The patient is a male aged 28 to 32, a dermatoscopic image of a skin lesion:
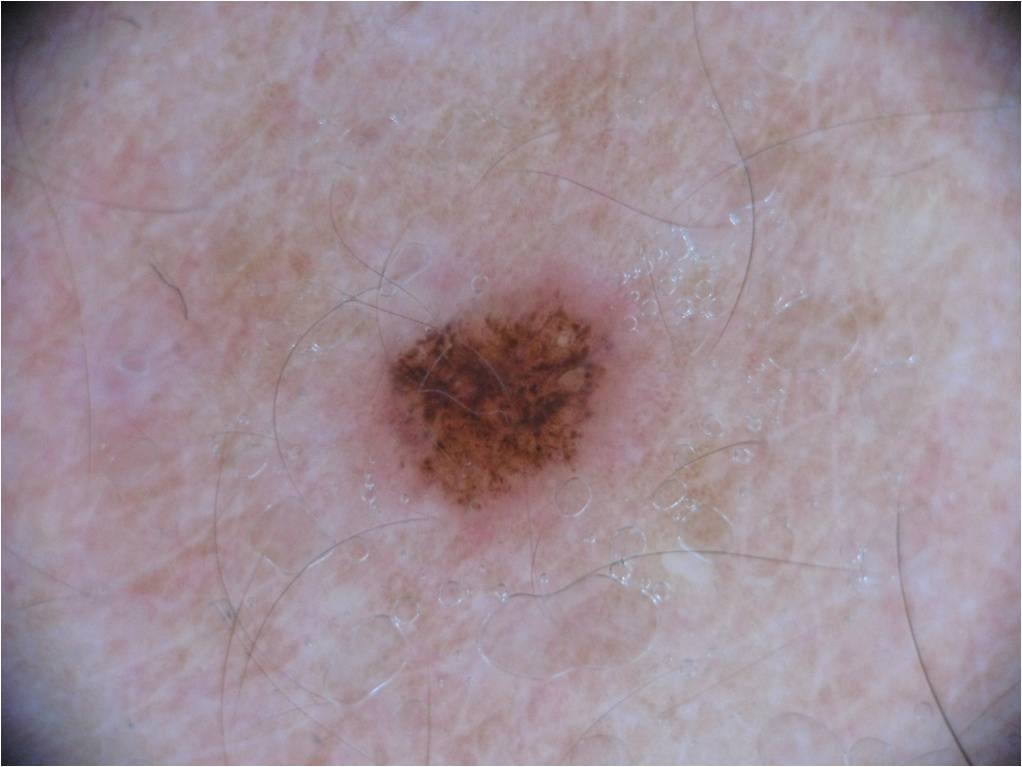As (left, top, right, bottom), the lesion spans [378,287,617,514]. Dermoscopic assessment notes globules, milia-like cysts, and pigment network; no streaks or negative network. The lesion is small relative to the field of view. Expert review diagnosed this as a melanocytic nevus, a benign skin lesion.